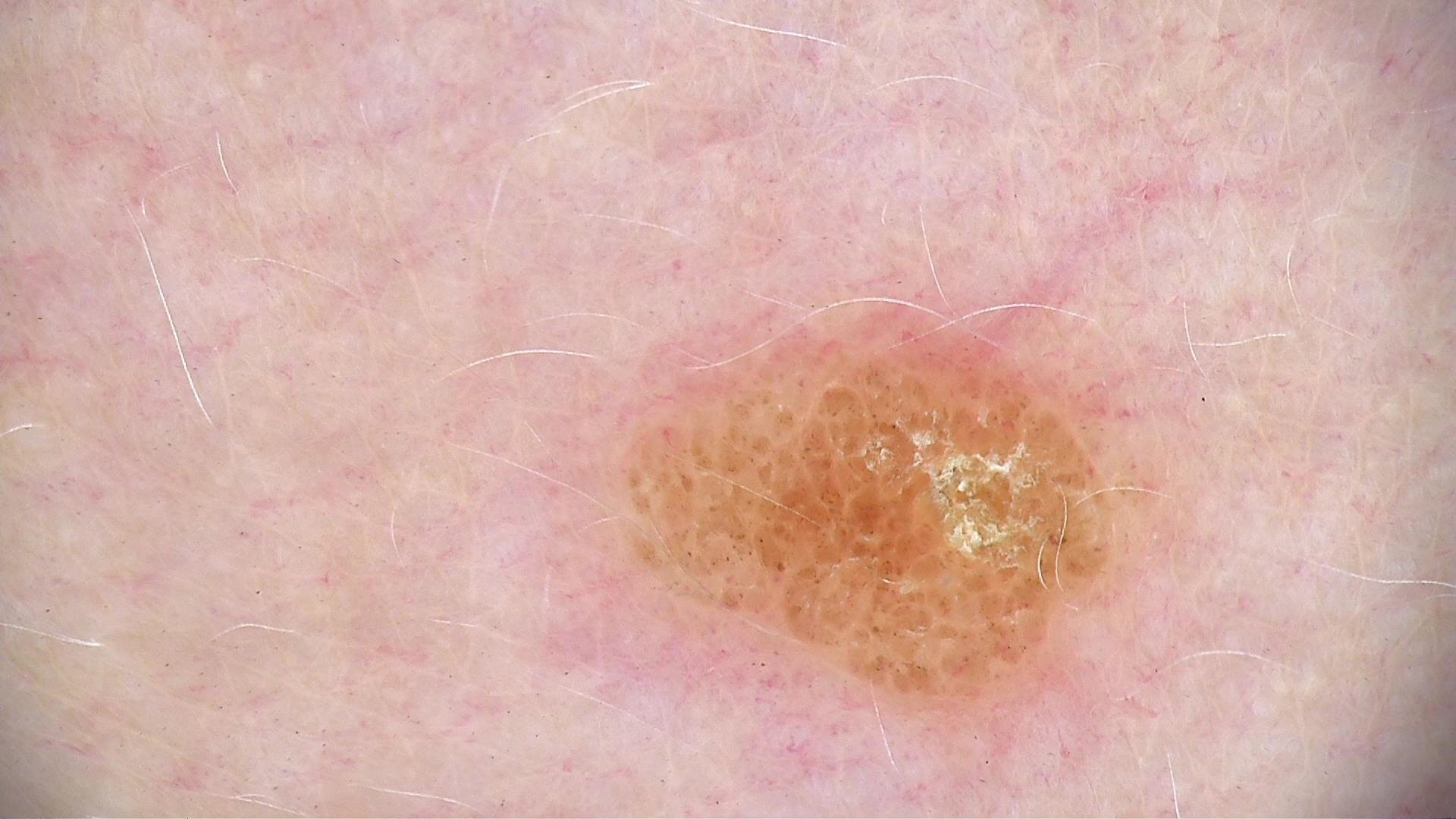{
  "image": "dermatoscopy",
  "lesion_type": {
    "main_class": "banal",
    "pattern": "compound"
  },
  "diagnosis": {
    "name": "compound nevus",
    "code": "cb",
    "malignancy": "benign",
    "super_class": "melanocytic",
    "confirmation": "expert consensus"
  }
}